Dermoscopy of a skin lesion: 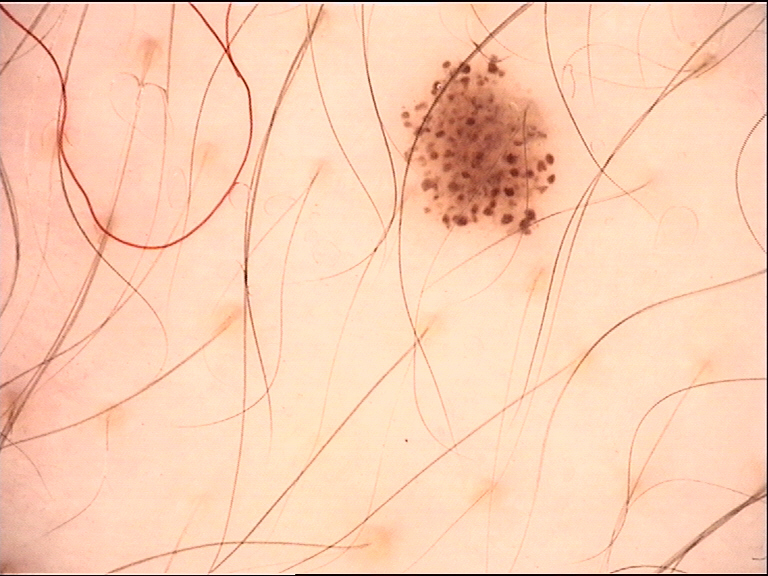class: dysplastic junctional nevus (expert consensus).